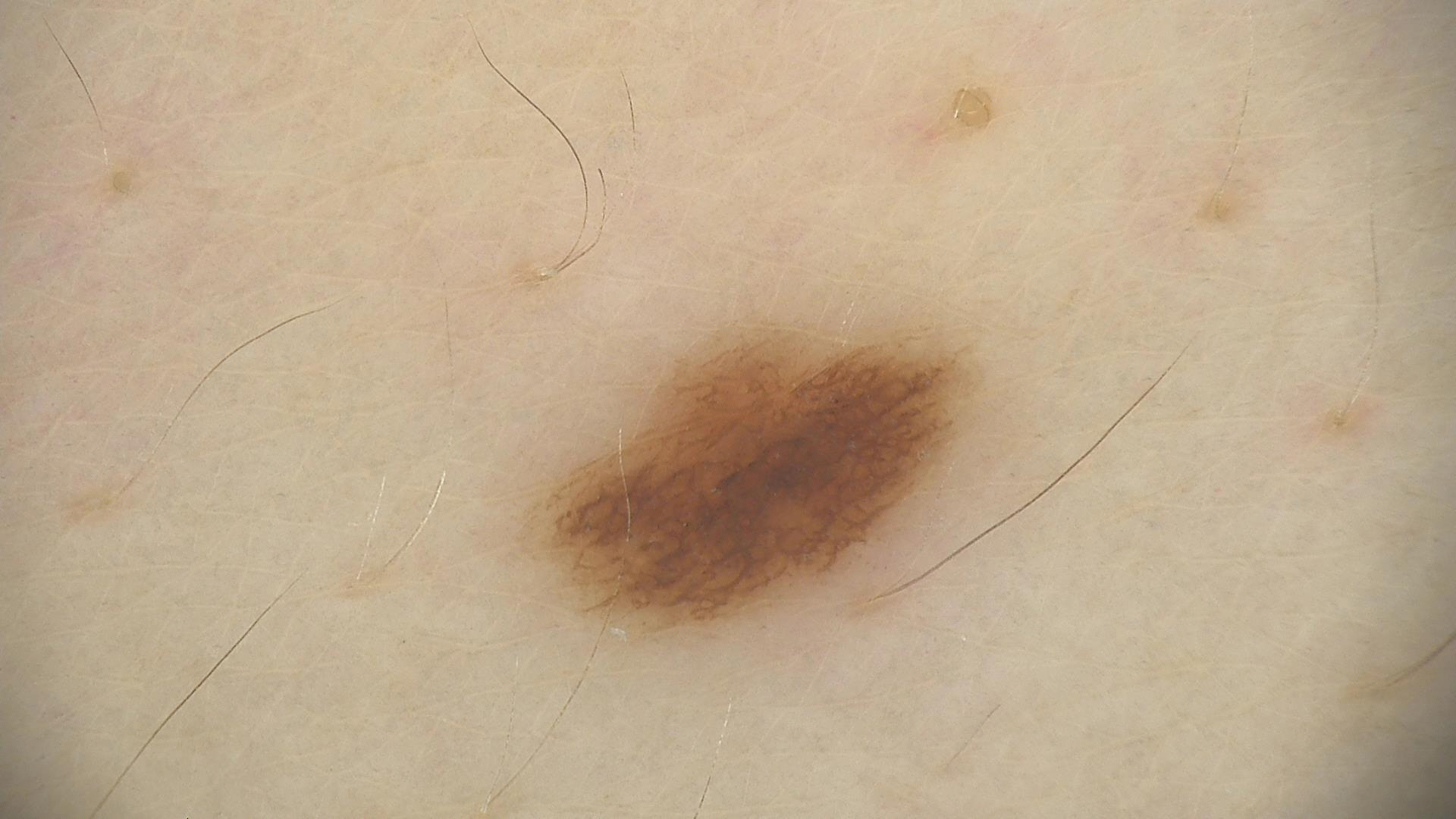modality: dermatoscopy | diagnosis: dysplastic junctional nevus (expert consensus).